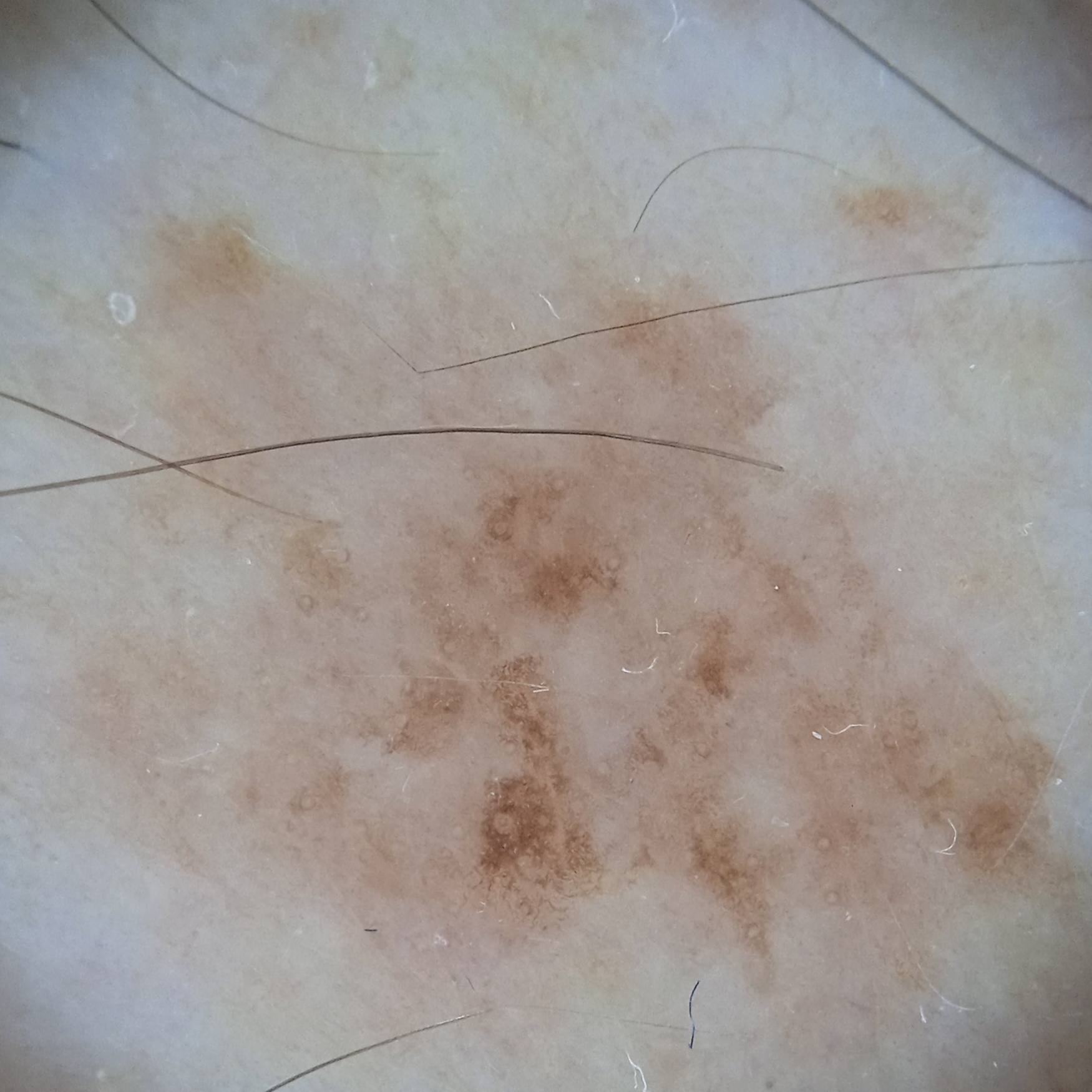assessment=melanoma (dermatologist consensus).